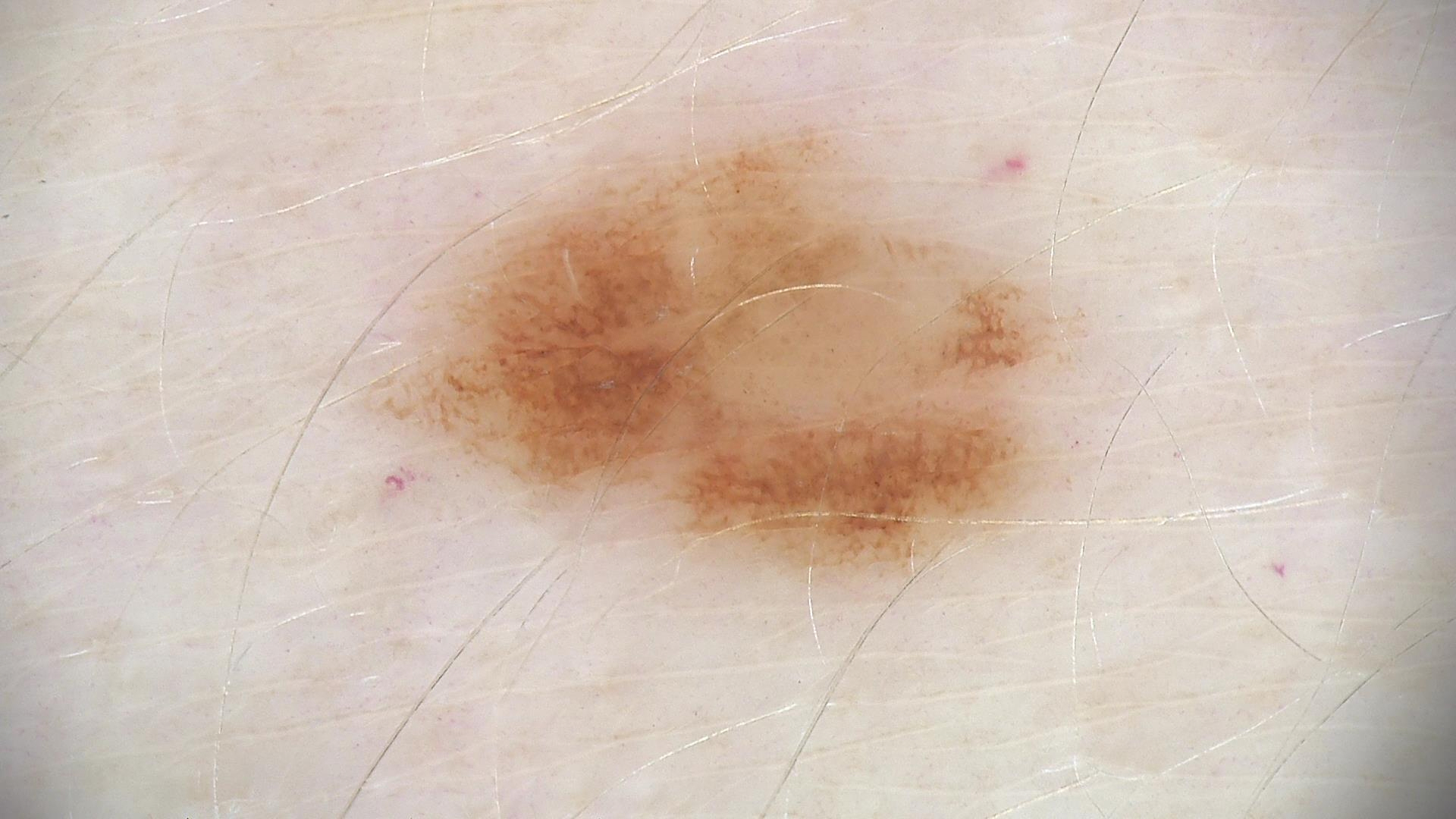image type: dermoscopy; class: dysplastic junctional nevus (expert consensus).